A skin lesion imaged with a dermatoscope.
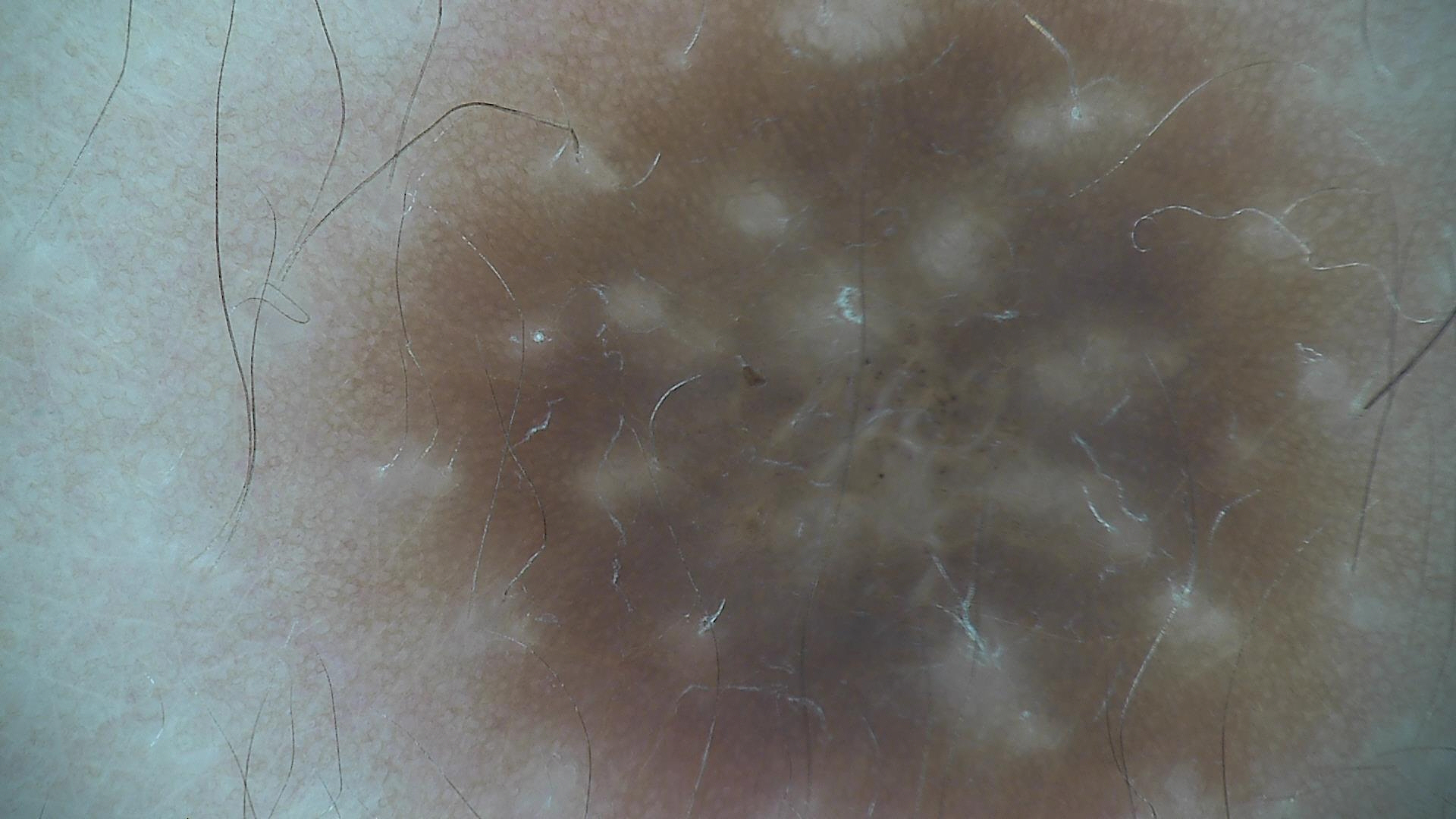The morphology is that of a fibro-histiocytic lesion.
Labeled as a benign lesion — a dermatofibroma.